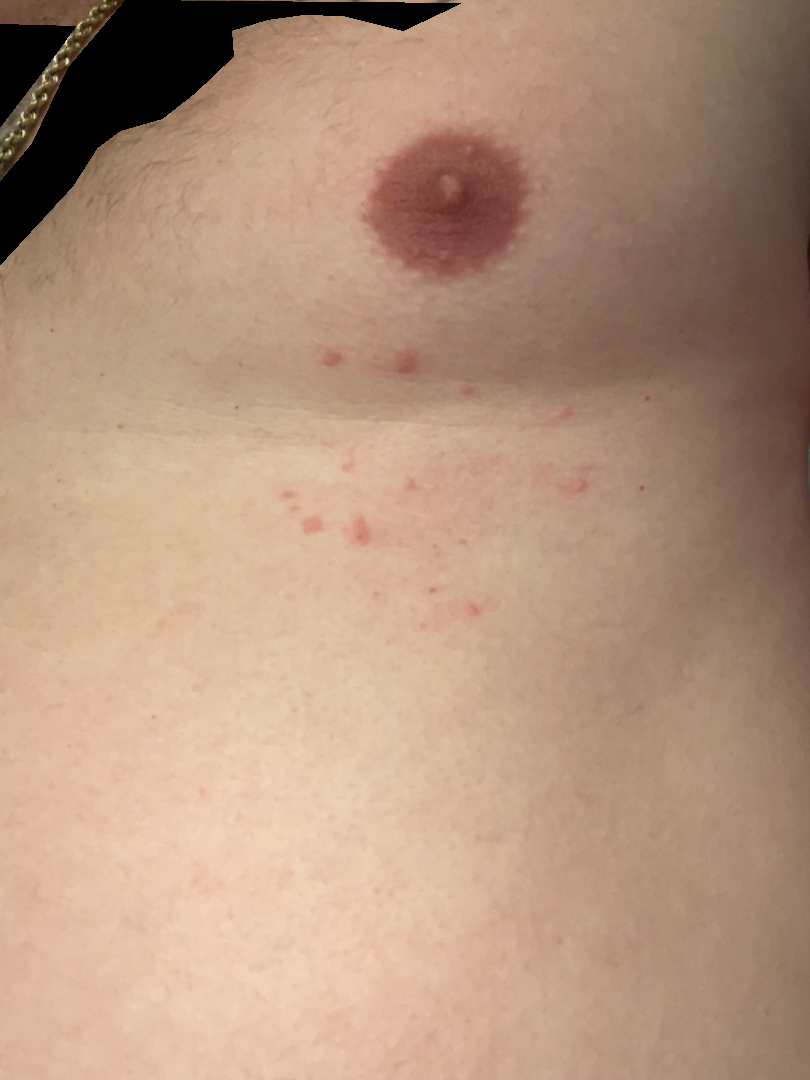affected area = front of the torso | view = close-up | skin tone = Fitzpatrick II | texture = raised or bumpy | subject = male, age 18–29 | onset = less than one week | symptoms = itching | patient's own categorization = a rash | dermatologist impression = three dermatologists each reviewed the case: the favored diagnosis is Folliculitis; also on the differential is Acne; with consideration of Acute dermatitis, NOS; less probable is Grover's disease; less likely is Irritant Contact Dermatitis; a remote consideration is Insect Bite.